Dermoscopy of a skin lesion.
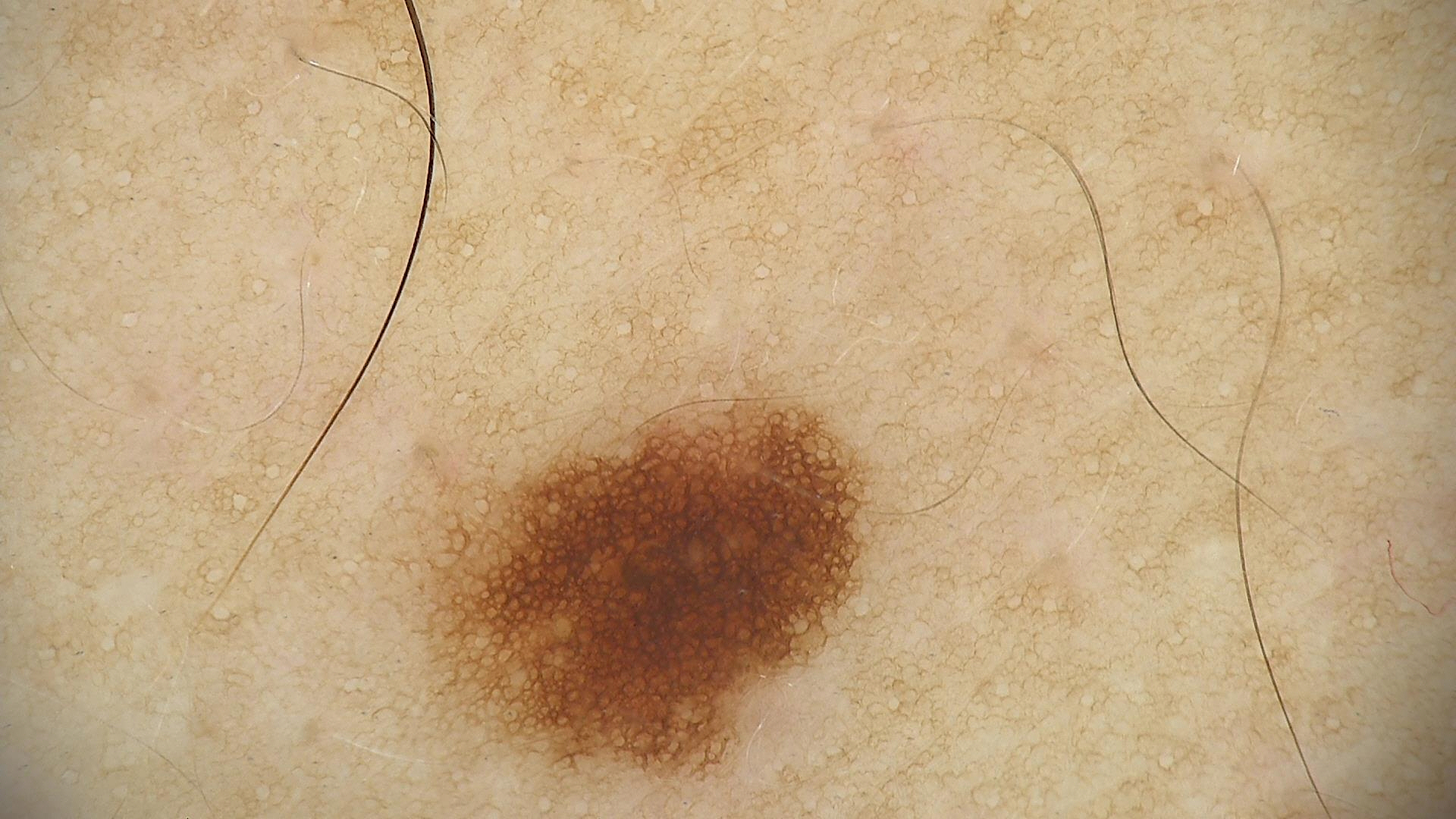The diagnosis was a dysplastic junctional nevus.